The patient is a female aged approximately 40, a dermatoscopic image of a skin lesion:
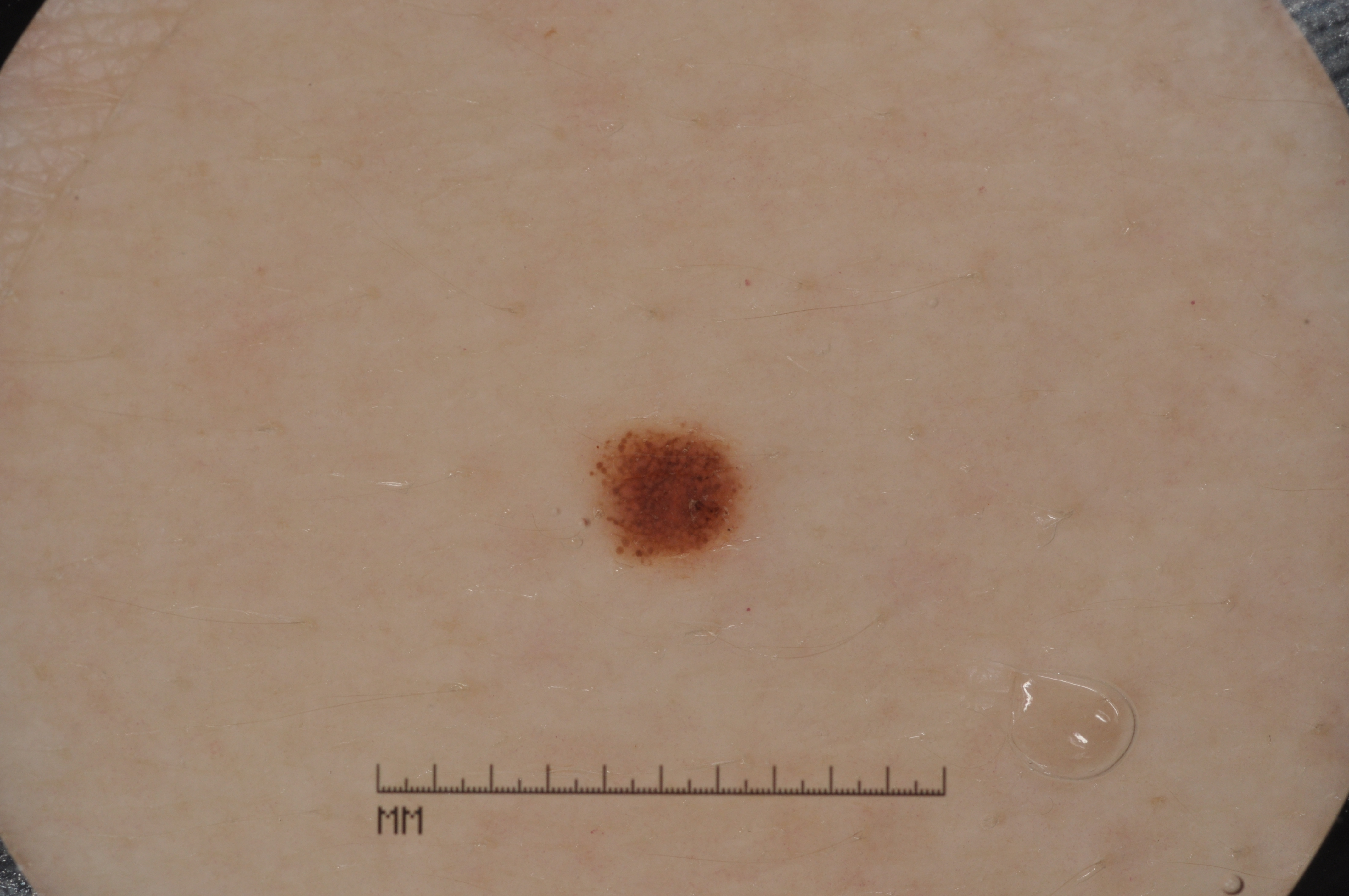Notes:
* lesion bbox: <box>590, 427, 748, 567</box>
* features: pigment network
* lesion size: ~1% of the field
* assessment: a melanocytic nevus, a benign lesion